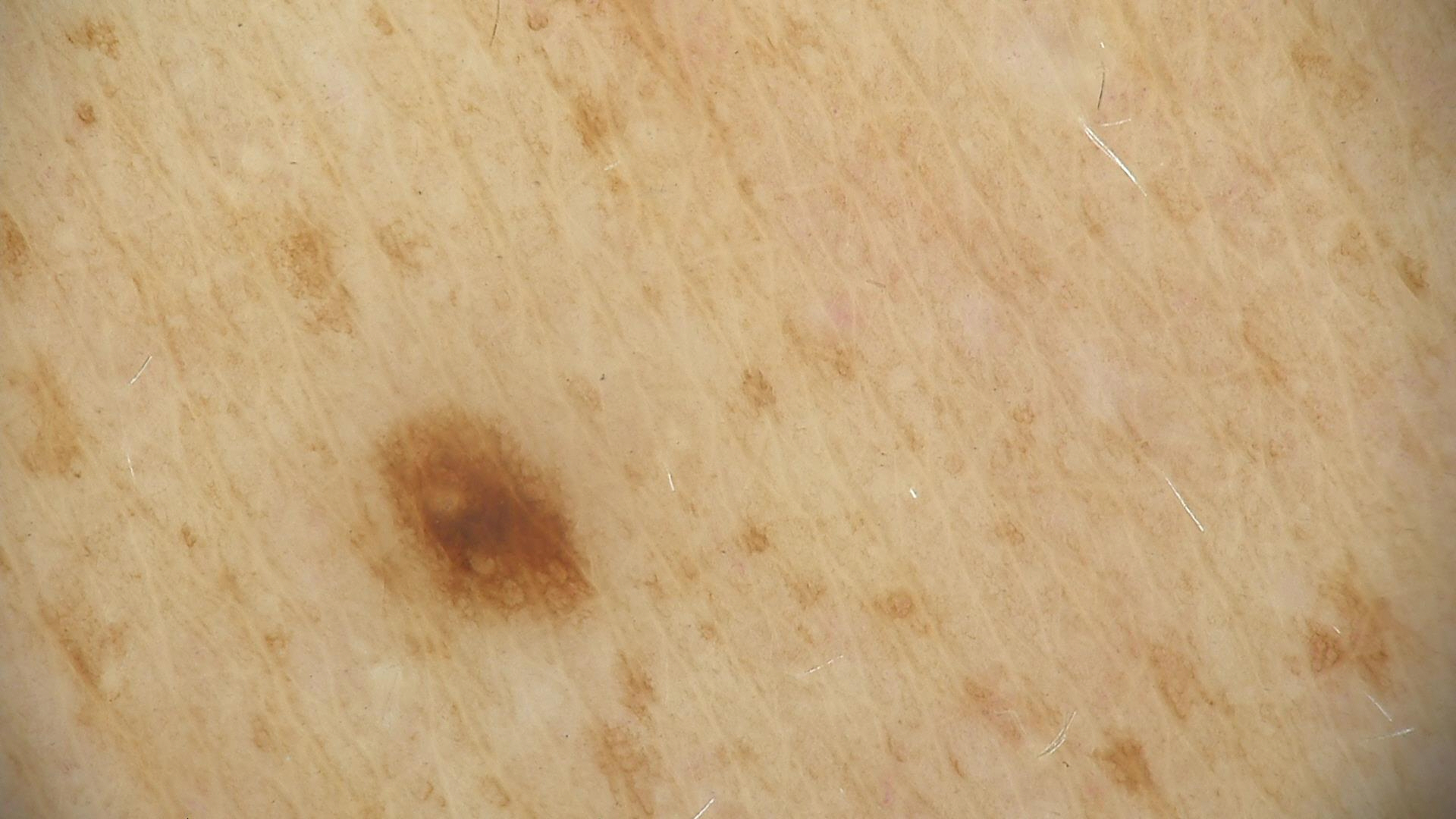Impression: Consistent with a dysplastic junctional nevus.